The patient says their skin reddens painfully with sun exposure · dermoscopy of a skin lesion · the patient describes having few moles overall · referred with a clinical suspicion of basal cell carcinoma:
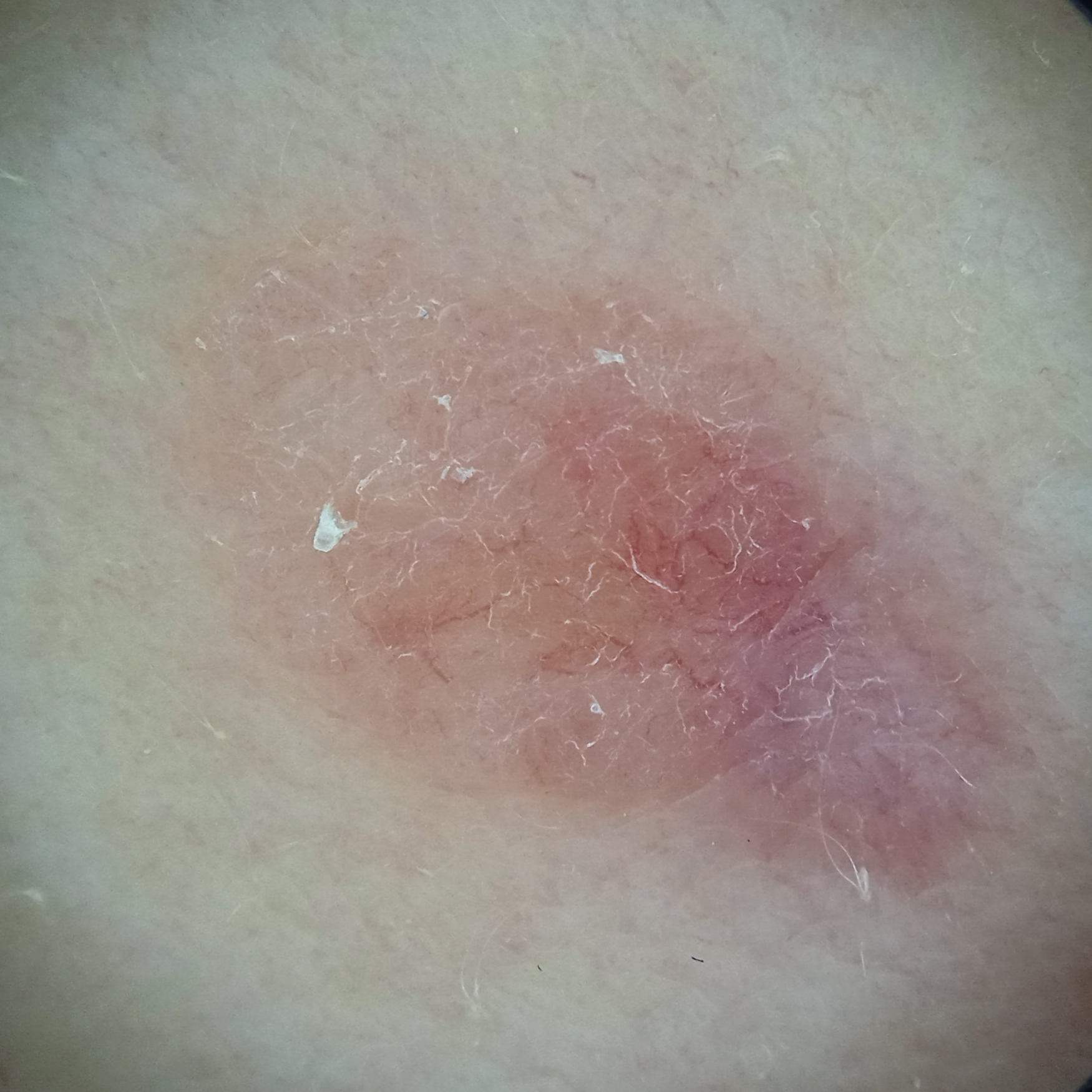<skin_lesion>
<lesion_location>the back</lesion_location>
<lesion_size>
<diameter_mm>12.3</diameter_mm>
</lesion_size>
<diagnosis>
<name>basal cell carcinoma</name>
<malignancy>malignant</malignancy>
<procedure>excision</procedure>
<tumor_thickness_mm>1.1</tumor_thickness_mm>
</diagnosis>
</skin_lesion>